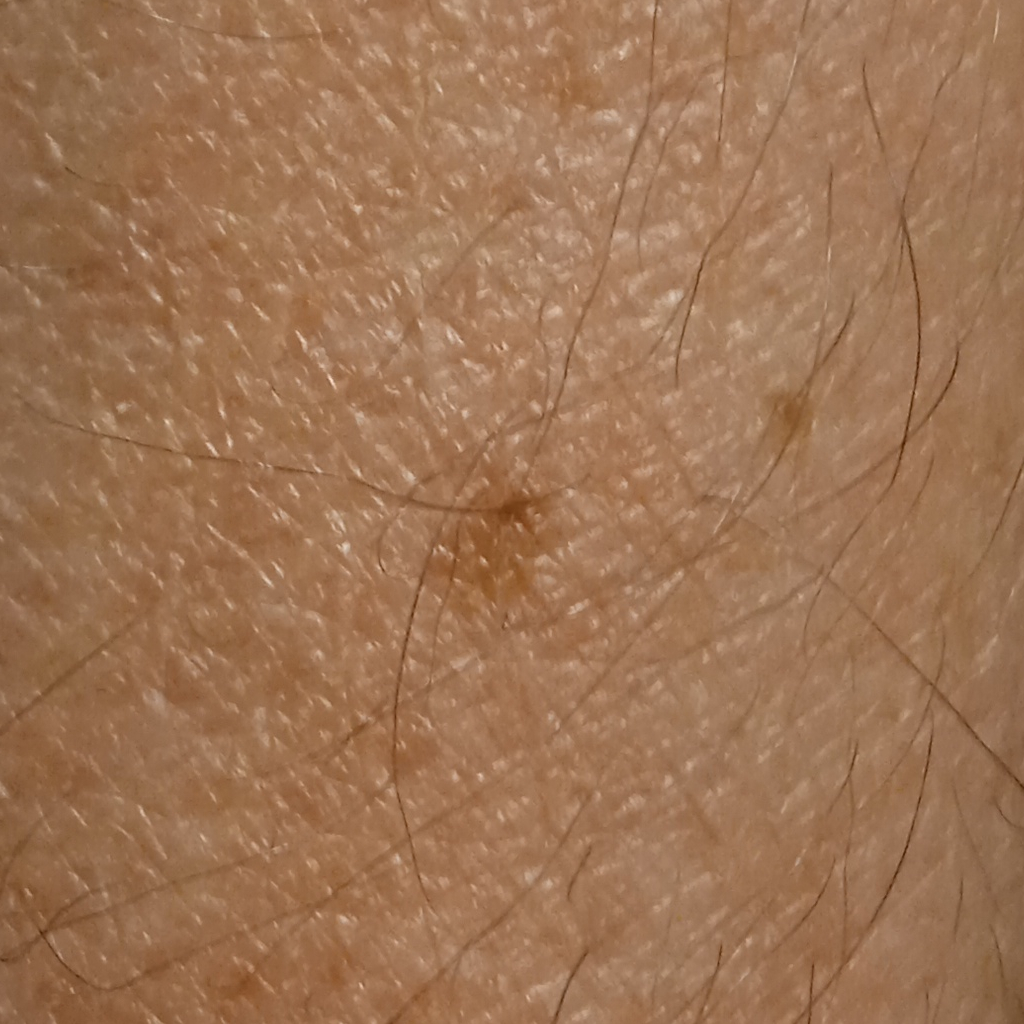Case:
– image: clinical photo
– clinical context: research study (no referral diagnosis)
– location: an arm
– lesion size: 4.2 mm
– assessment: seborrheic keratosis (dermatologist consensus)